By history, prior skin cancer (patient or family) and prior malignancy (patient or family). A female patient in their 90s. A clinical close-up photograph of a skin lesion. The patient is Fitzpatrick skin type II.
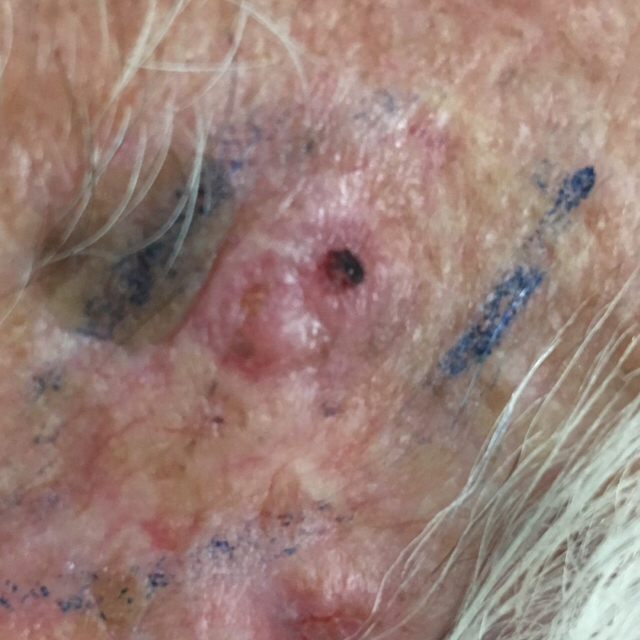The lesion is roughly 20 by 14 mm.
Confirmed on histopathology as a basal cell carcinoma.